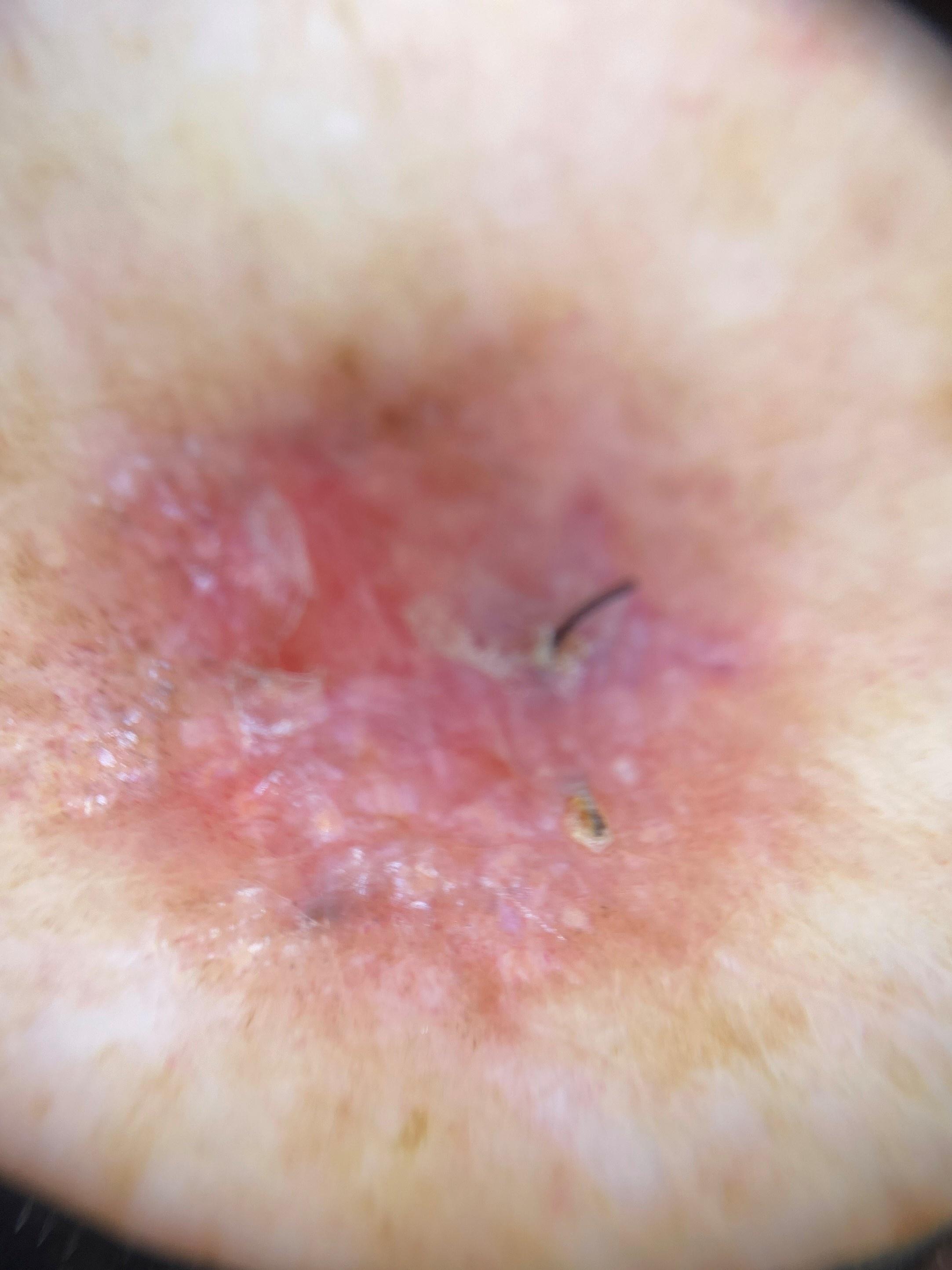Clinical context: A male patient roughly 80 years of age. A skin lesion imaged with contact-polarized dermoscopy. Recorded as skin type II. The lesion is on a lower extremity. Diagnosis: Histopathological examination showed a tumor of follicular differentiation — a basal cell carcinoma.